This image was taken at a distance:
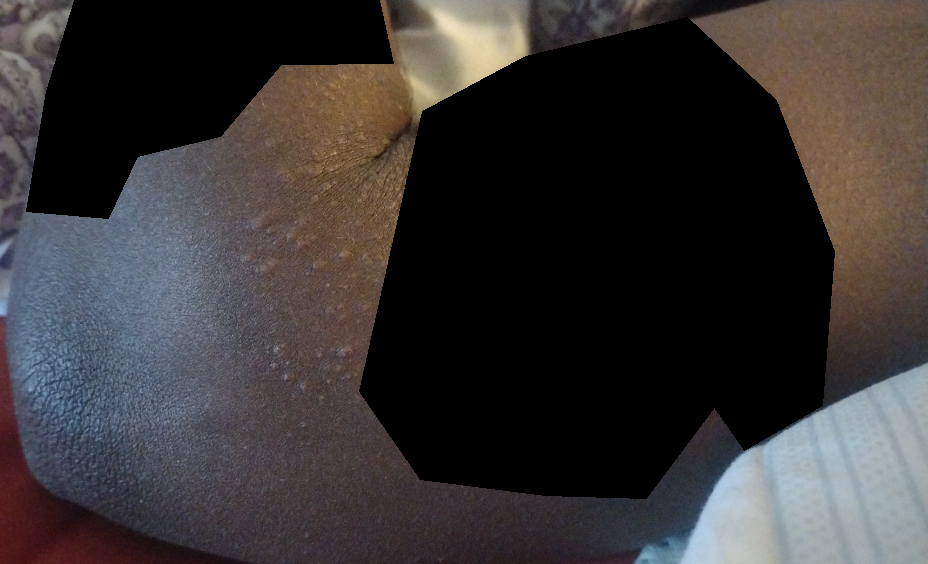On remote review of the image, the favored diagnosis is Lichen nitidus; an alternative is Eczema; less likely is Keratosis pilaris.